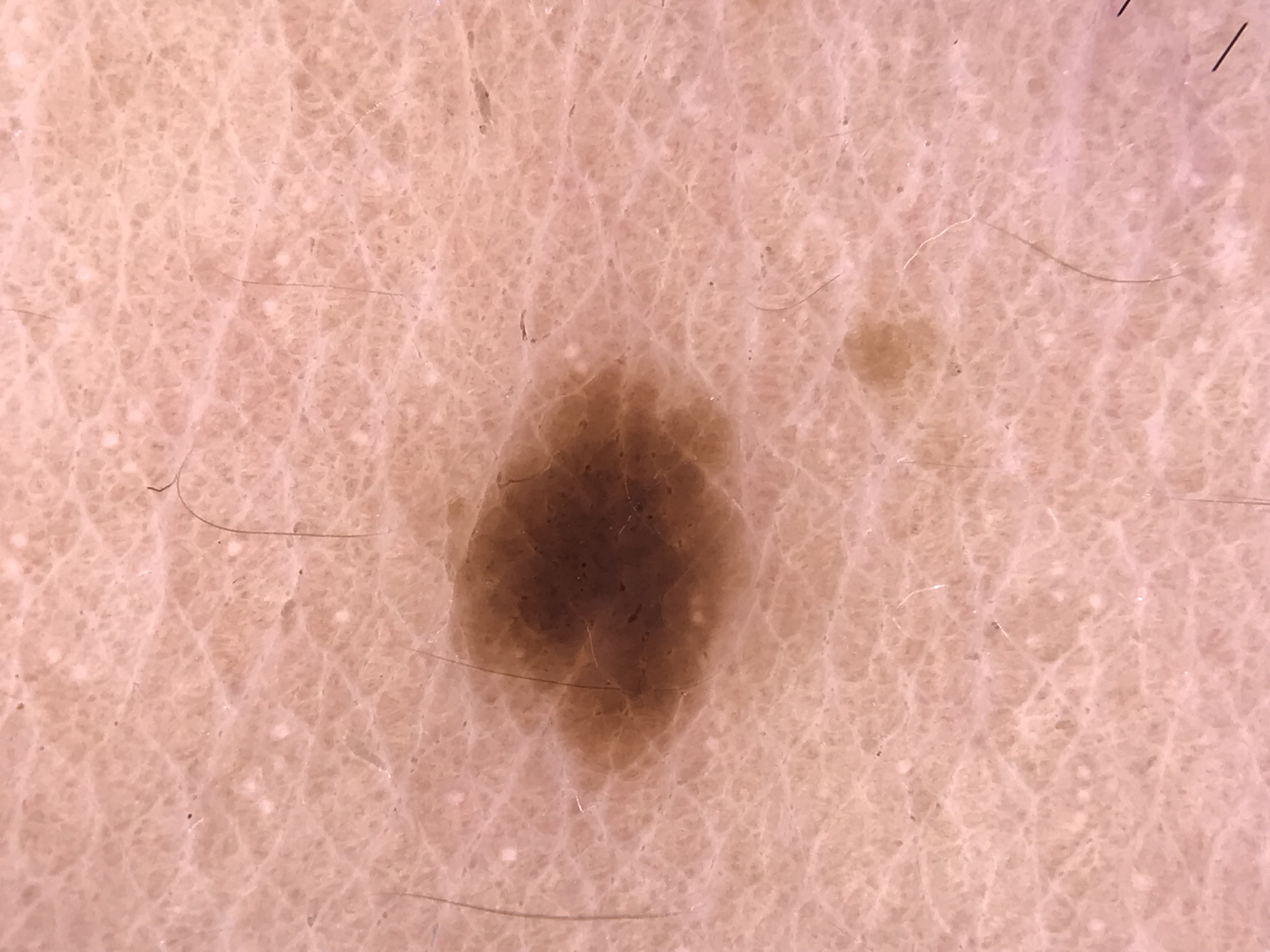Findings:
* assessment: junctional nevus (expert consensus)